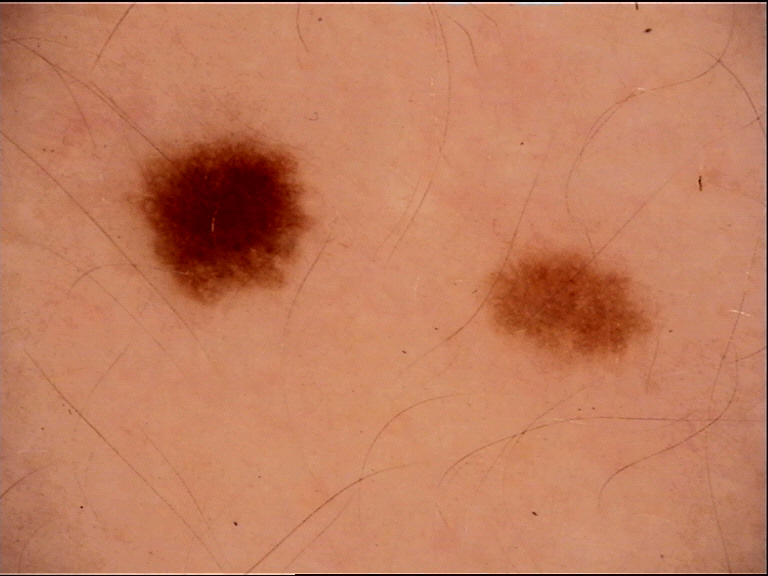{"diagnosis": {"name": "dysplastic junctional nevus", "code": "jd", "malignancy": "benign", "super_class": "melanocytic", "confirmation": "expert consensus"}}